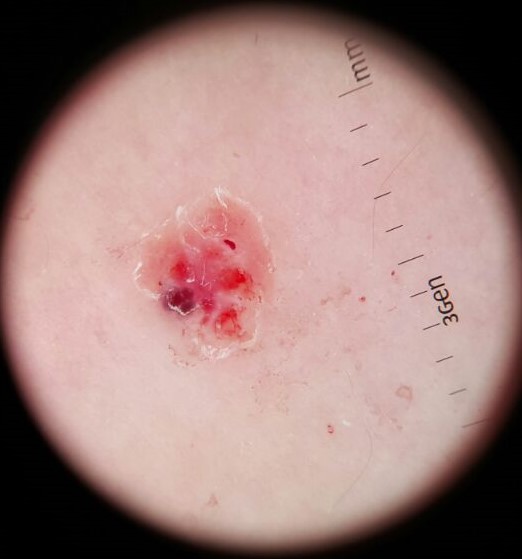assessment — angiokeratoma (expert consensus)